A dermoscopy image of a single skin lesion.
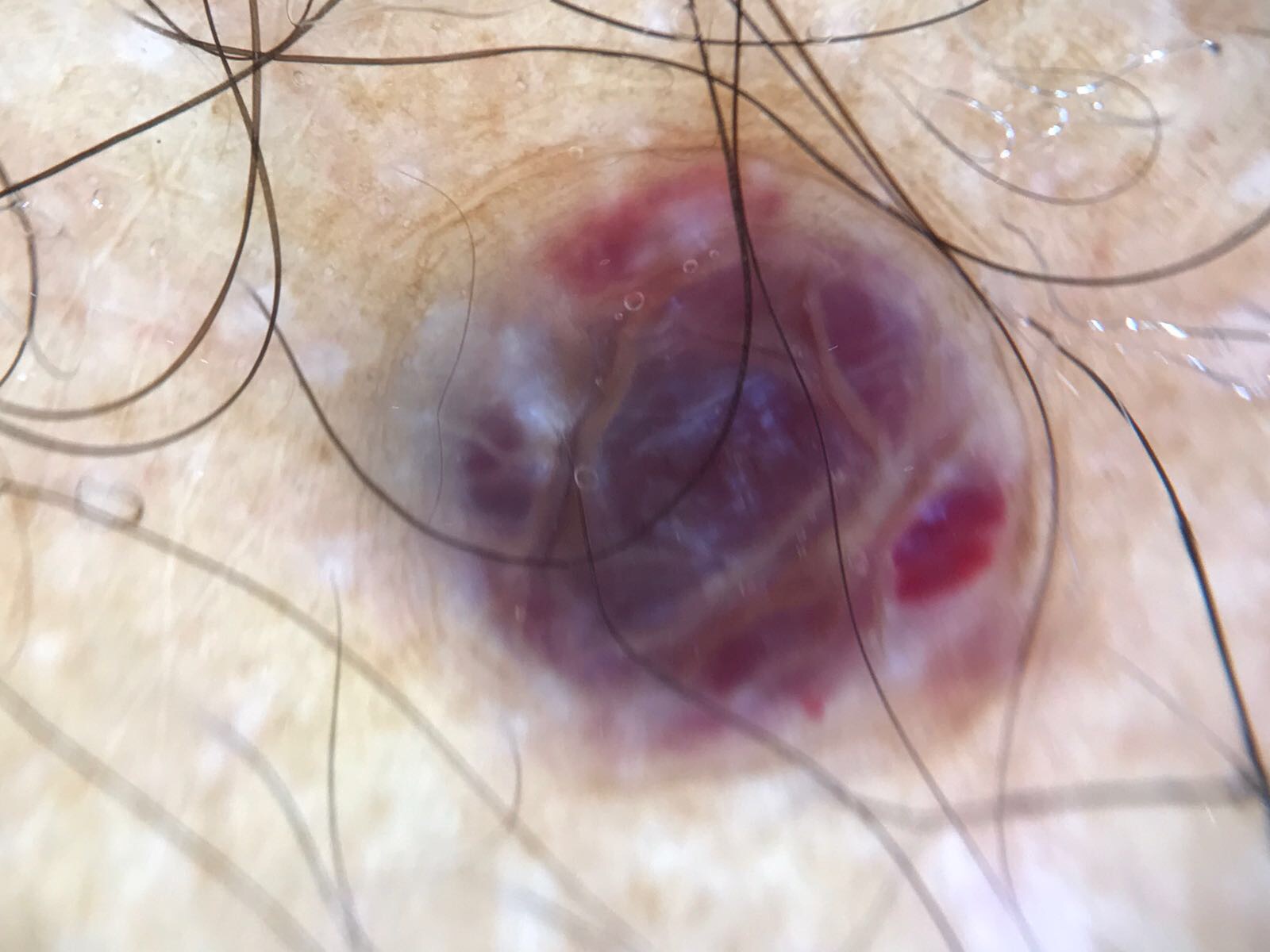Classified as a benign lesion — a hemangioma.